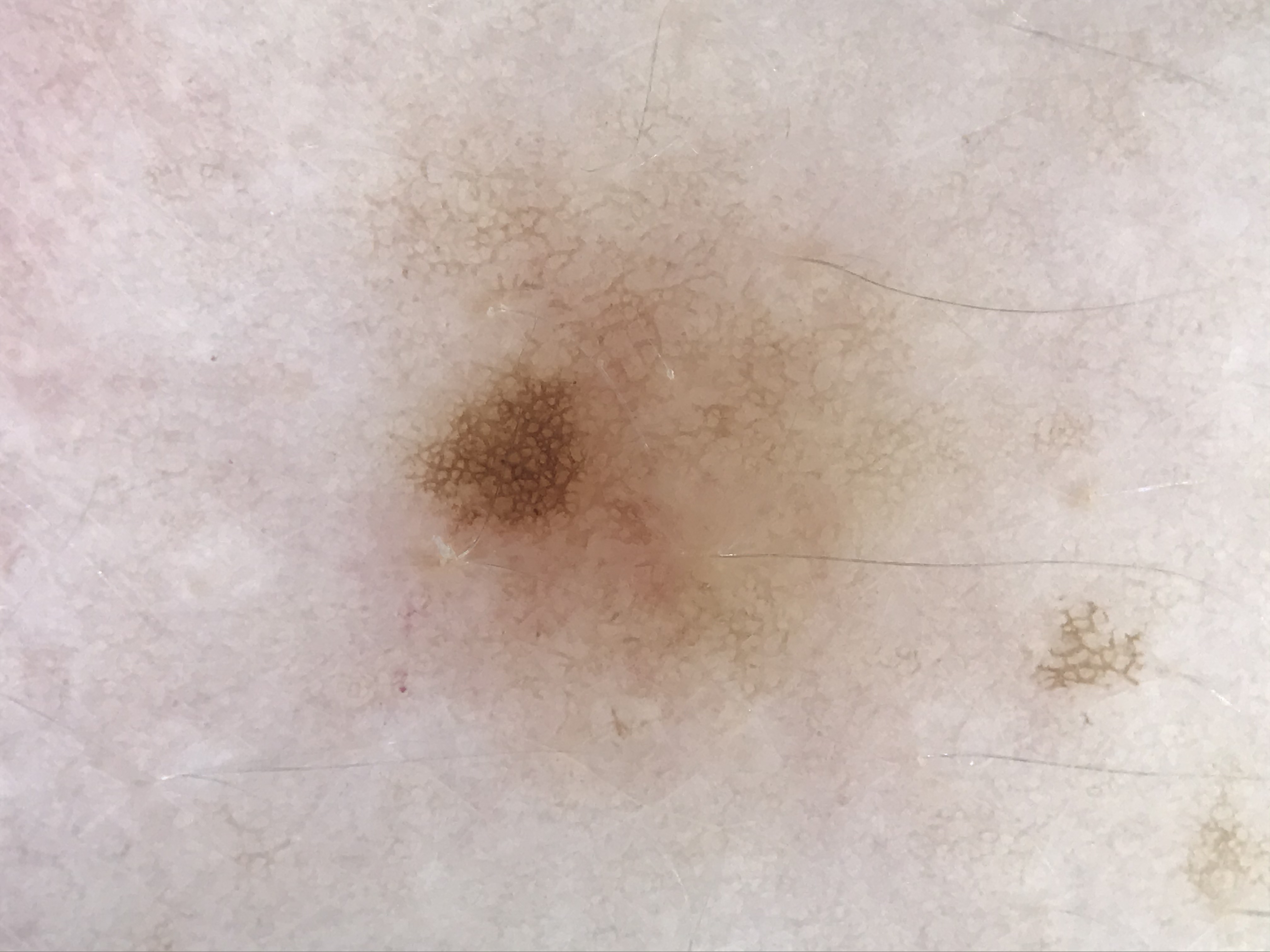{"diagnosis": {"name": "lentigo simplex", "code": "ls", "malignancy": "benign", "super_class": "melanocytic", "confirmation": "expert consensus"}}